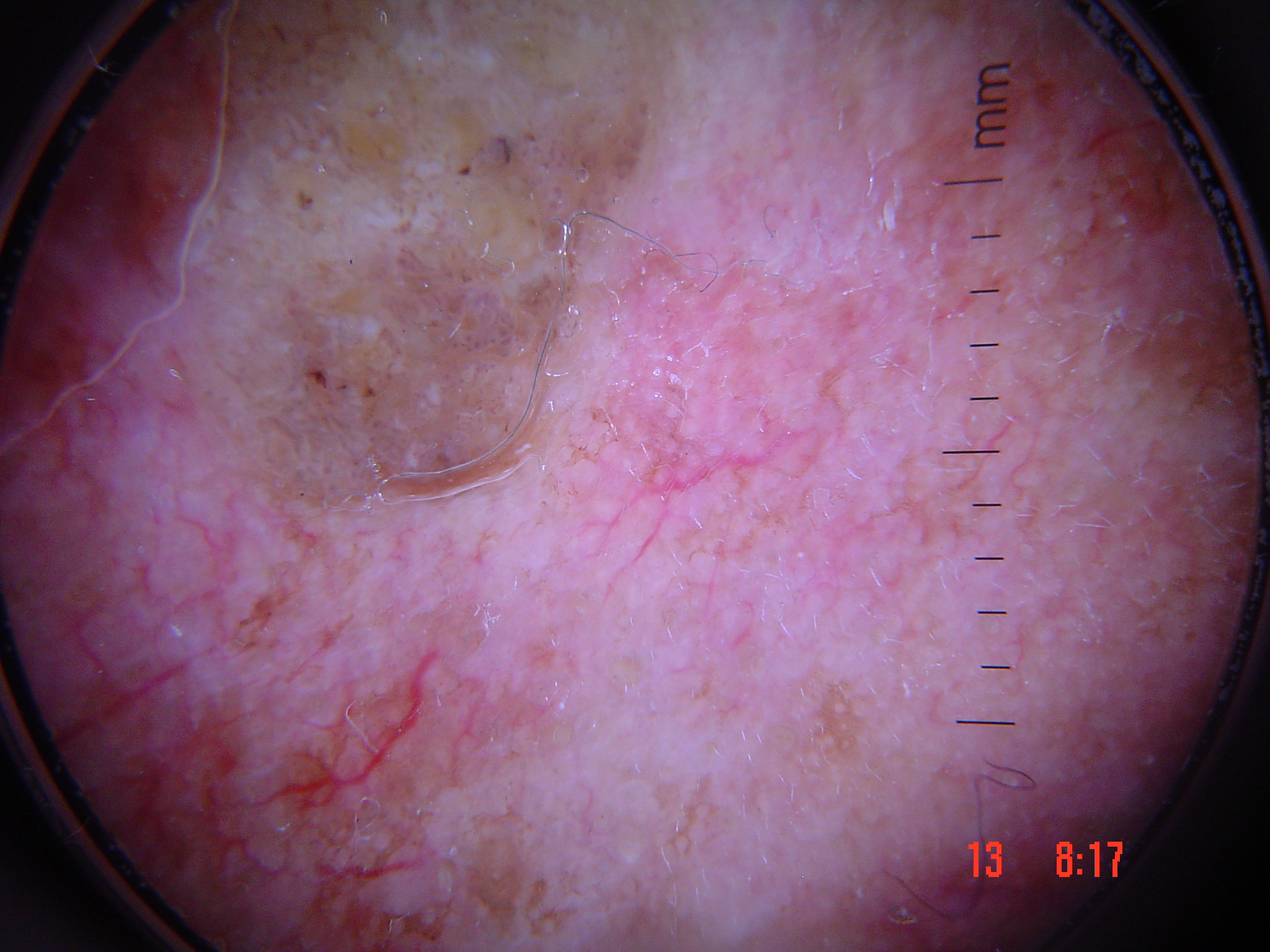A dermoscopy image of a single skin lesion. Classified as a benign lesion — a seborrheic keratosis.